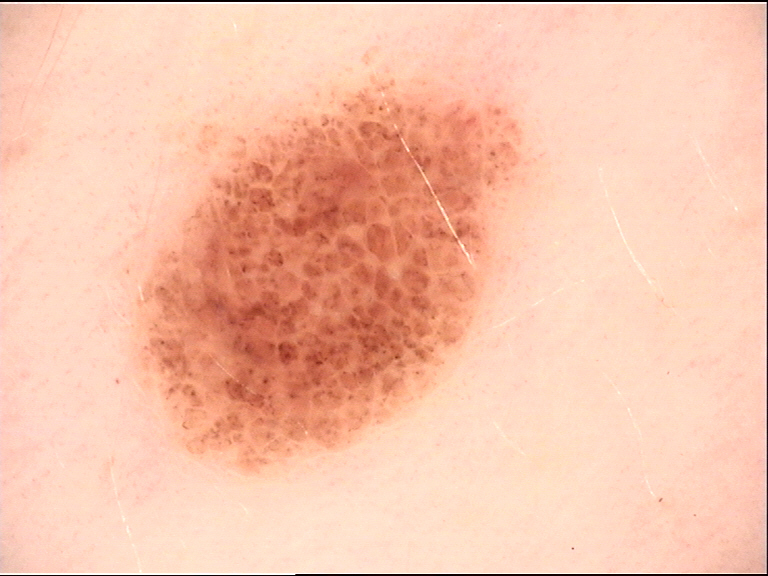Consistent with a junctional nevus.